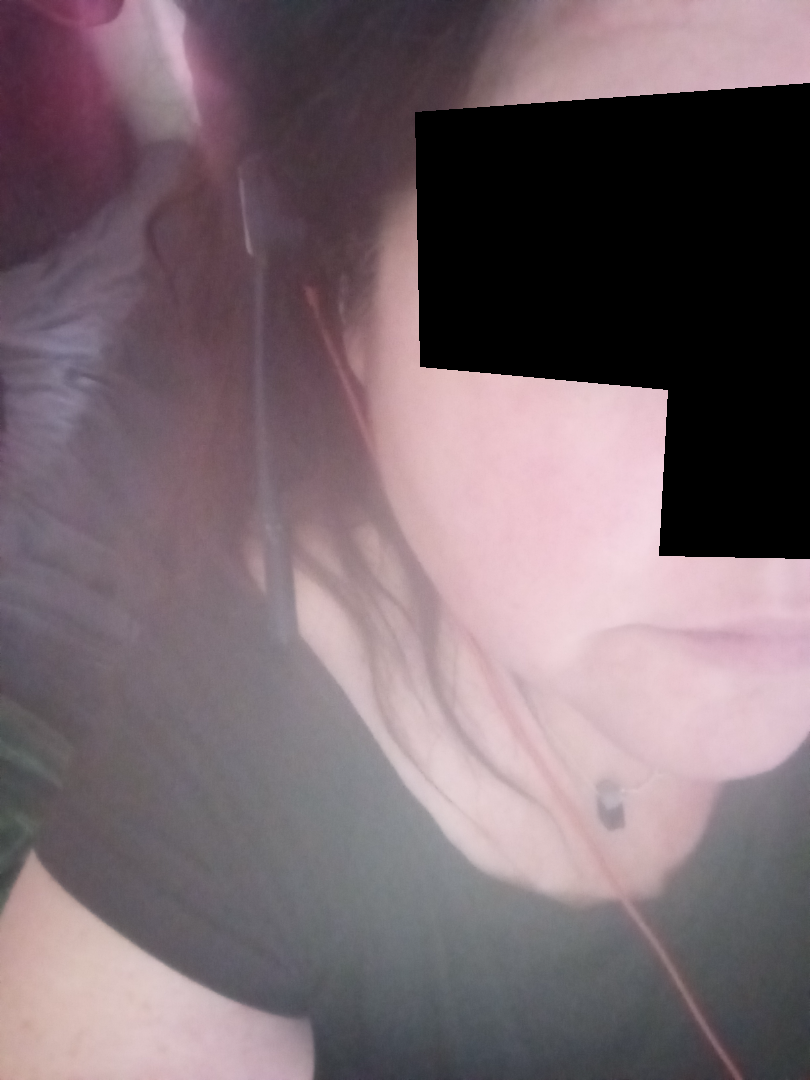Assessment:
No differential diagnosis could be assigned on photographic review.
Clinical context:
The lesion is described as raised or bumpy and fluid-filled. Female patient, age 50–59. Self-categorized by the patient as skin that appeared healthy to them. No constitutional symptoms were reported. Located on the head or neck. Present for less than one week. An image taken at an angle.